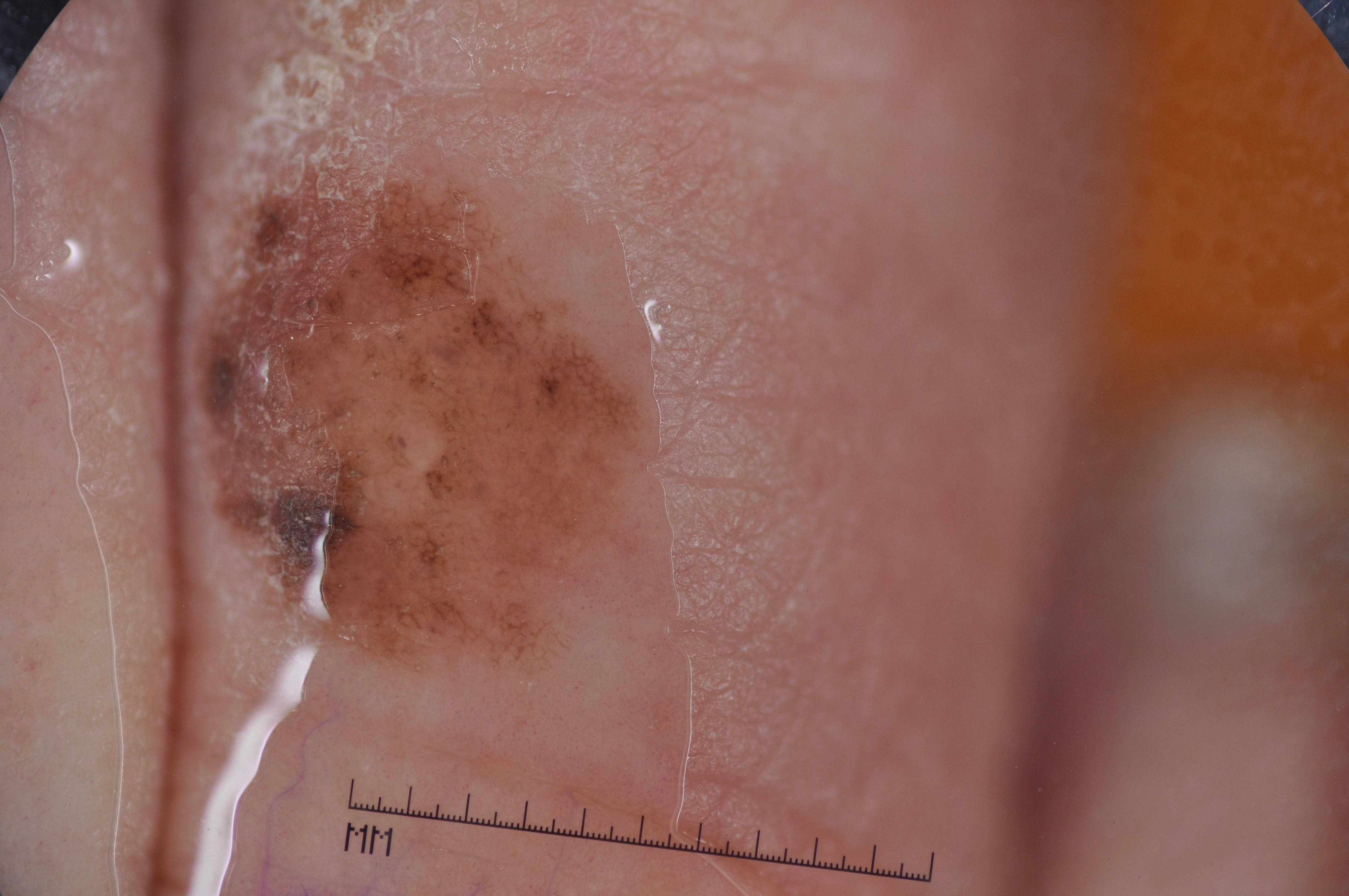Image and clinical context:
A skin lesion imaged with a dermatoscope. The subject is a male approximately 70 years of age. The dermoscopic pattern shows pigment network. The lesion occupies the region left=191, top=142, right=654, bottom=694.
Conclusion:
The clinical diagnosis was a melanocytic nevus, a benign skin lesion.